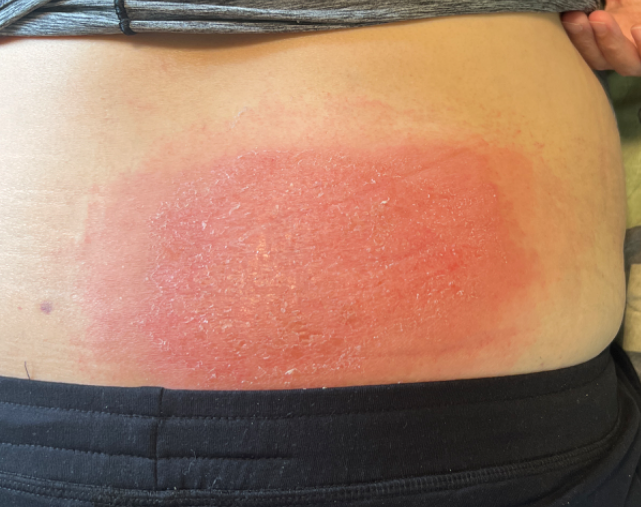Q: What conditions are considered?
A: the primary impression is Cellulitis; an alternative is Allergic Contact Dermatitis; possibly Erythema migrans